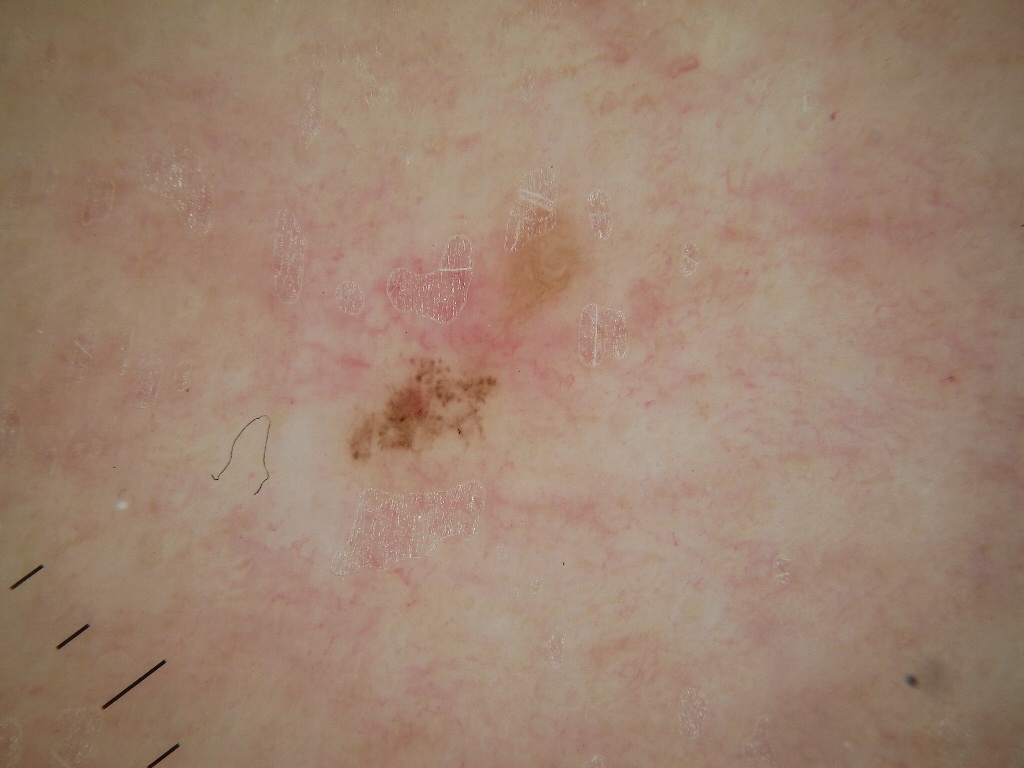Findings: This is a dermoscopic photograph of a skin lesion. The subject is a female in their 50s. The lesion spans x1=338, y1=346, x2=518, y2=474. On dermoscopy, the lesion shows no pigment network, globules, negative network, streaks, or milia-like cysts. Assessment: Diagnosed as a melanocytic nevus.